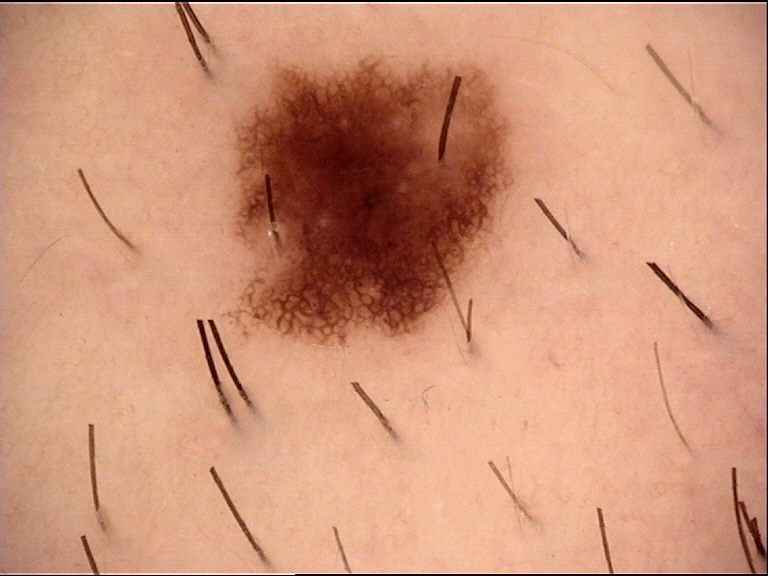Impression:
Classified as a dysplastic junctional nevus.